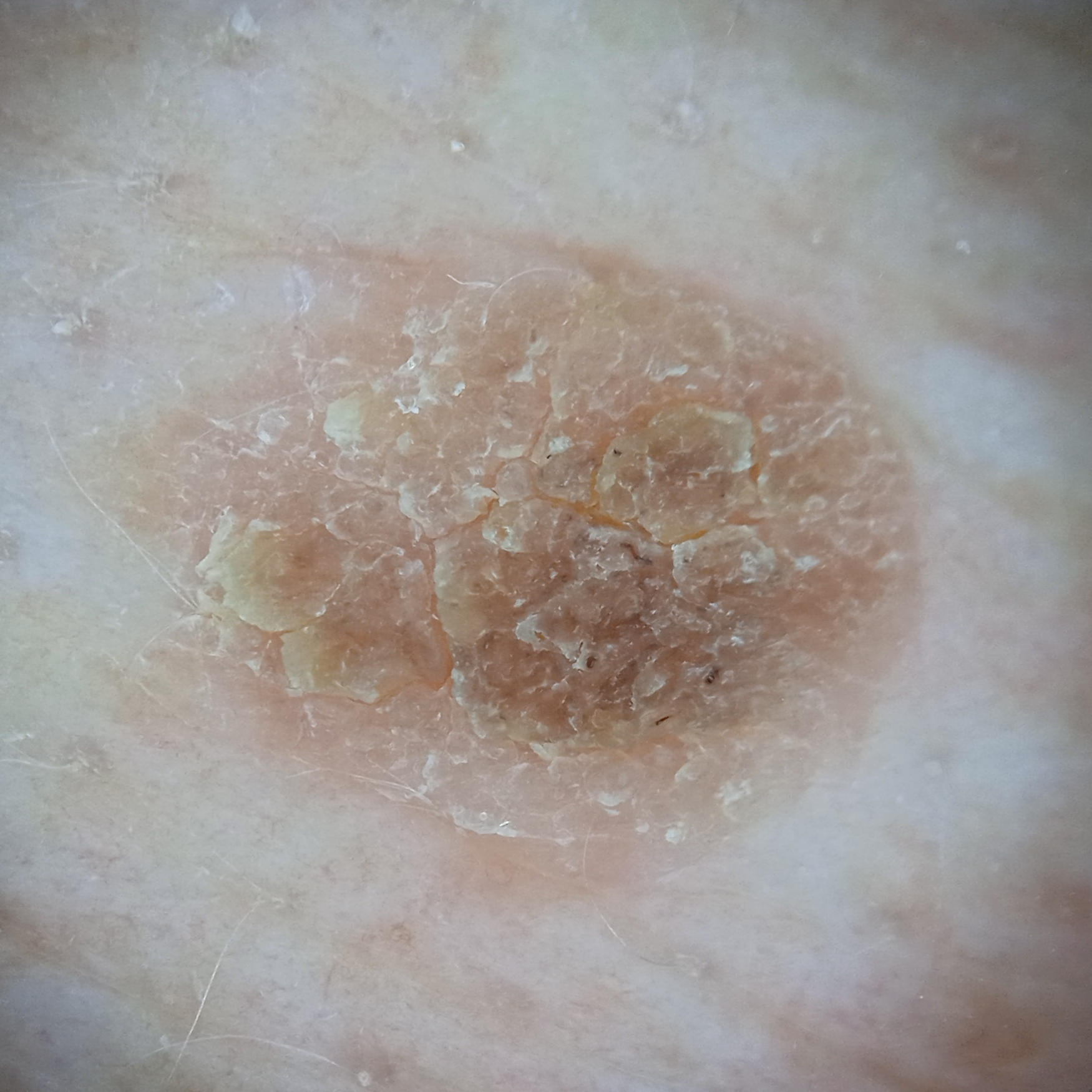The lesion was assessed as a seborrheic keratosis.